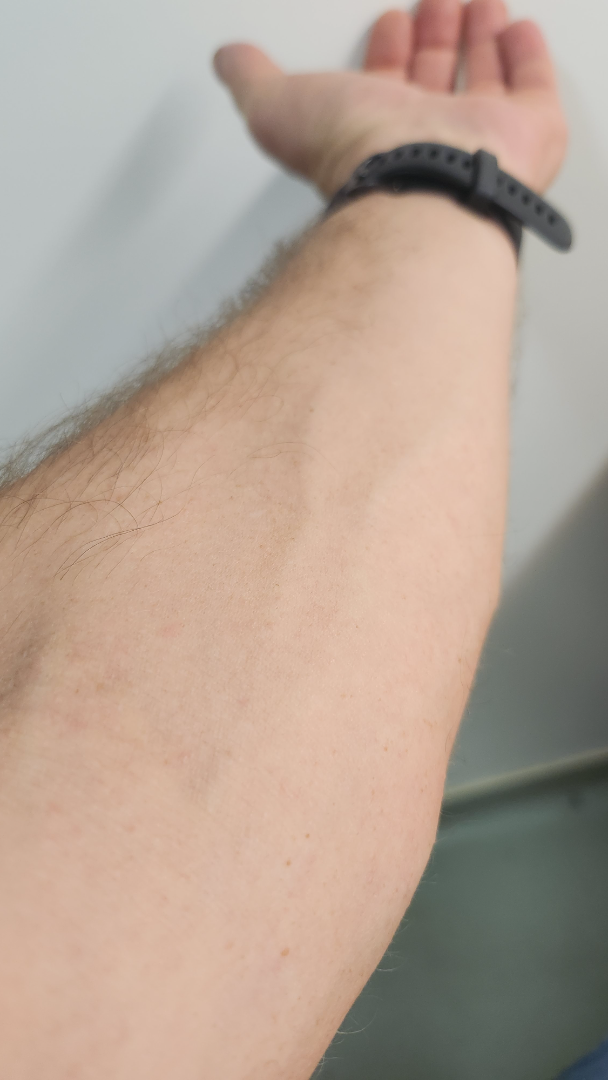<summary>
<assessment>unable to determine</assessment>
</summary>